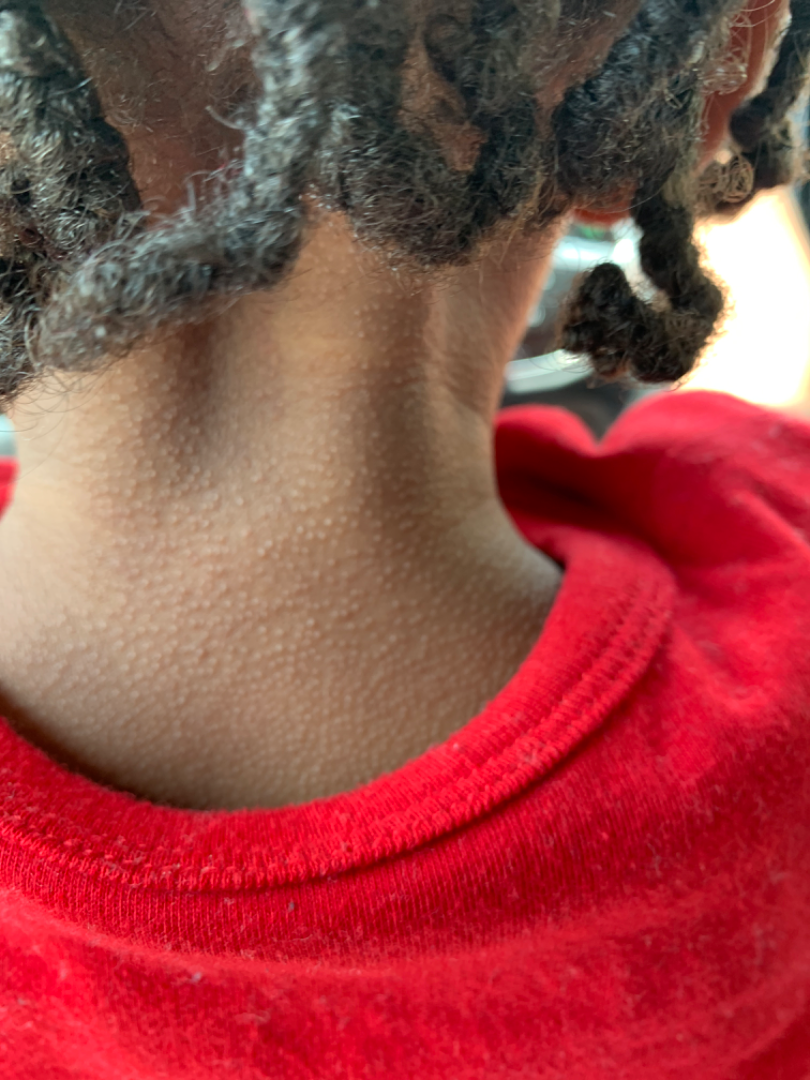  assessment: unable to determine
  body_site:
    - arm
    - leg
    - head or neck
    - front of the torso
    - back of the torso
  shot_type: close-up